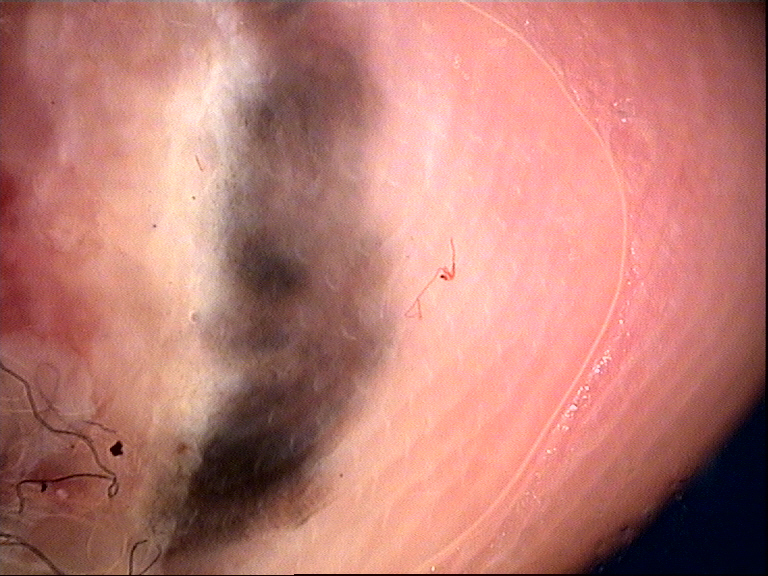Q: What kind of image is this?
A: dermoscopy
Q: What is the diagnosis?
A: acral nodular melanoma (biopsy-proven)